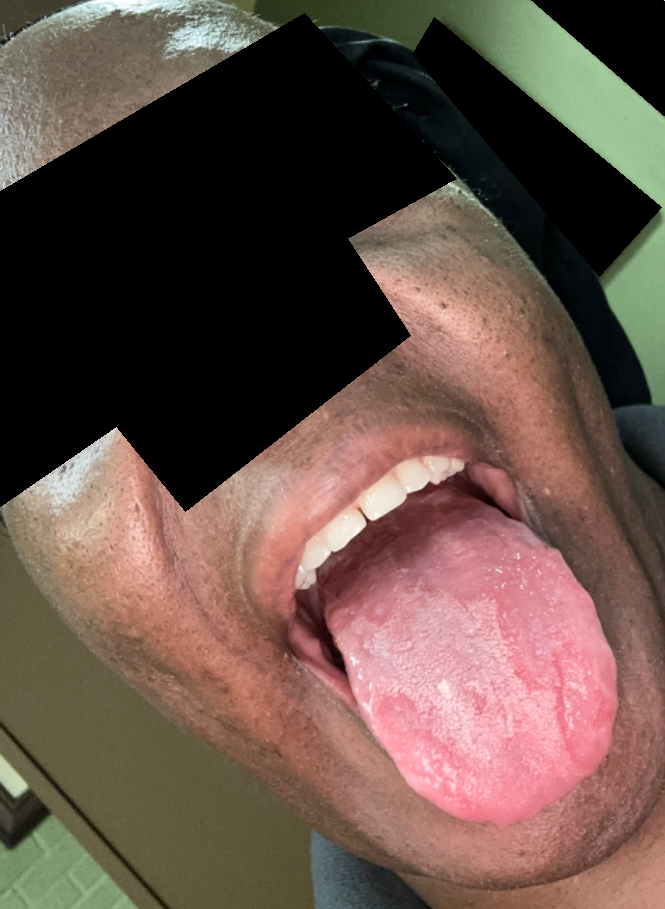Case summary:
- reported symptoms: none reported
- duration: less than one week
- subject: female, age 40–49
- described texture: raised or bumpy
- image framing: at an angle
- assessment: favoring Geographic tongue; with consideration of Atrophic glossitis; also on the differential is Lichen planus/lichenoid eruption